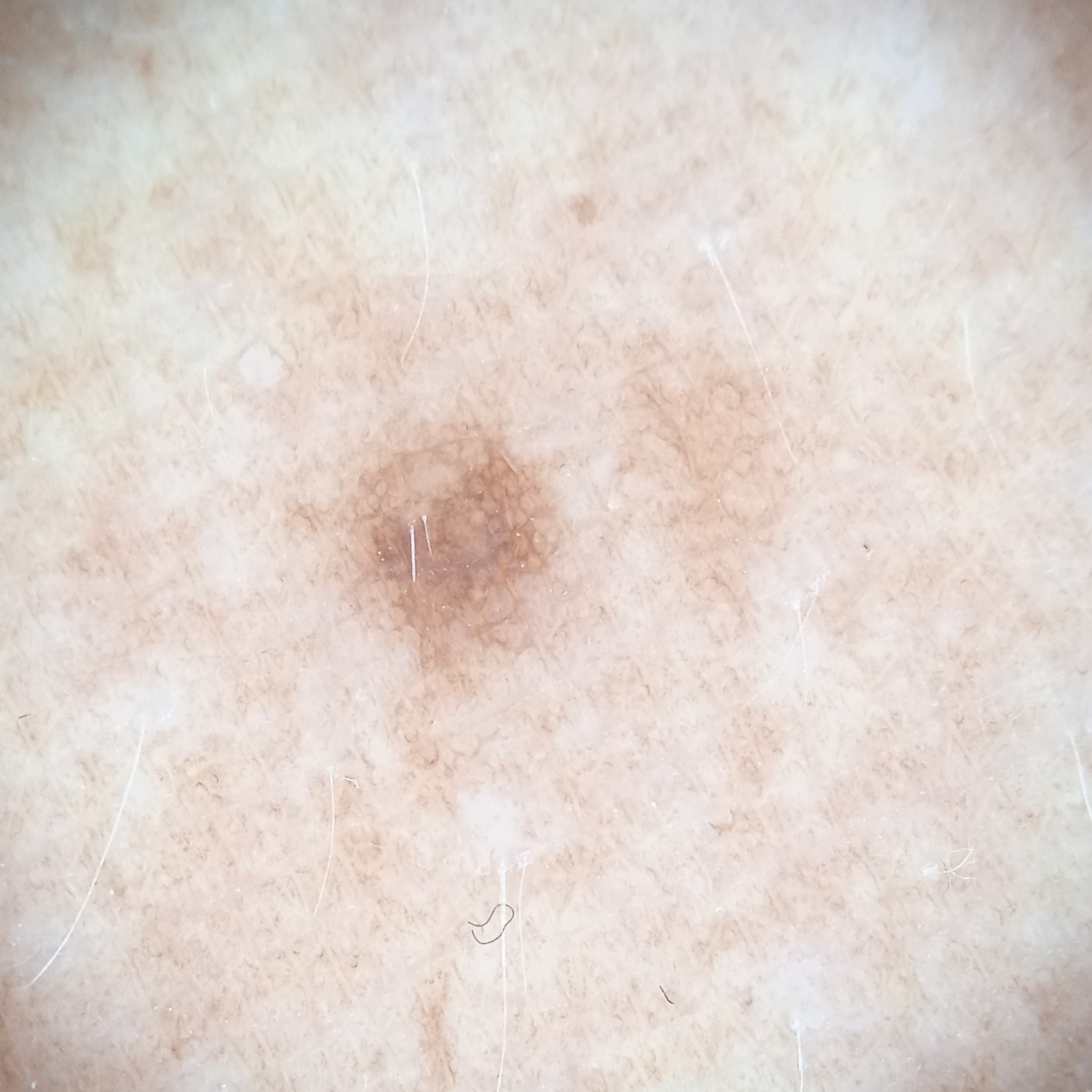* sun reaction — skin tans without first burning
* relevant history — a personal history of cancer
* size — 2.9 mm
* diagnostic label — melanocytic nevus (dermatologist consensus)